The lesion involves the arm, this is a close-up image.
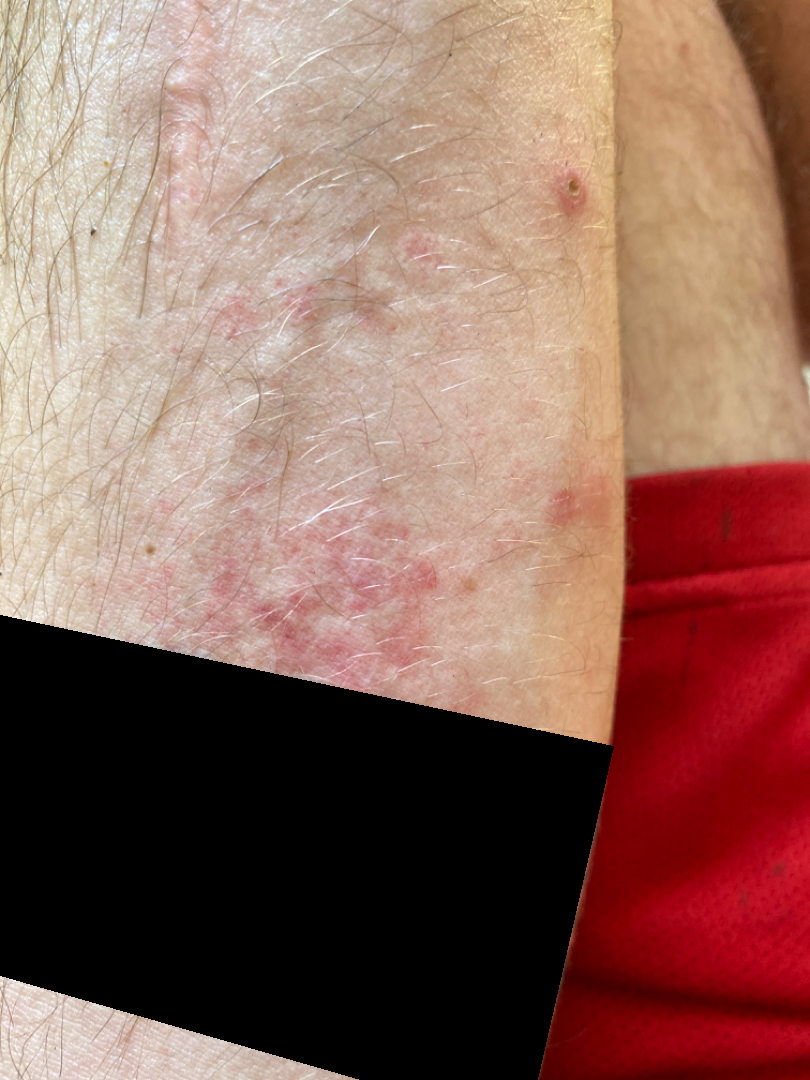{
  "assessment": "could not be assessed",
  "duration": "about one day",
  "texture": "flat",
  "symptoms": [
    "itching",
    "burning"
  ],
  "systemic_symptoms": "none reported"
}